Reported duration is less than one week. The patient reported no systemic symptoms. The patient described the issue as a rash. Close-up view. The affected area is the back of the torso and front of the torso. Female patient, age 60–69. Fitzpatrick phototype I. The lesion is described as raised or bumpy. Symptoms reported: bothersome appearance:
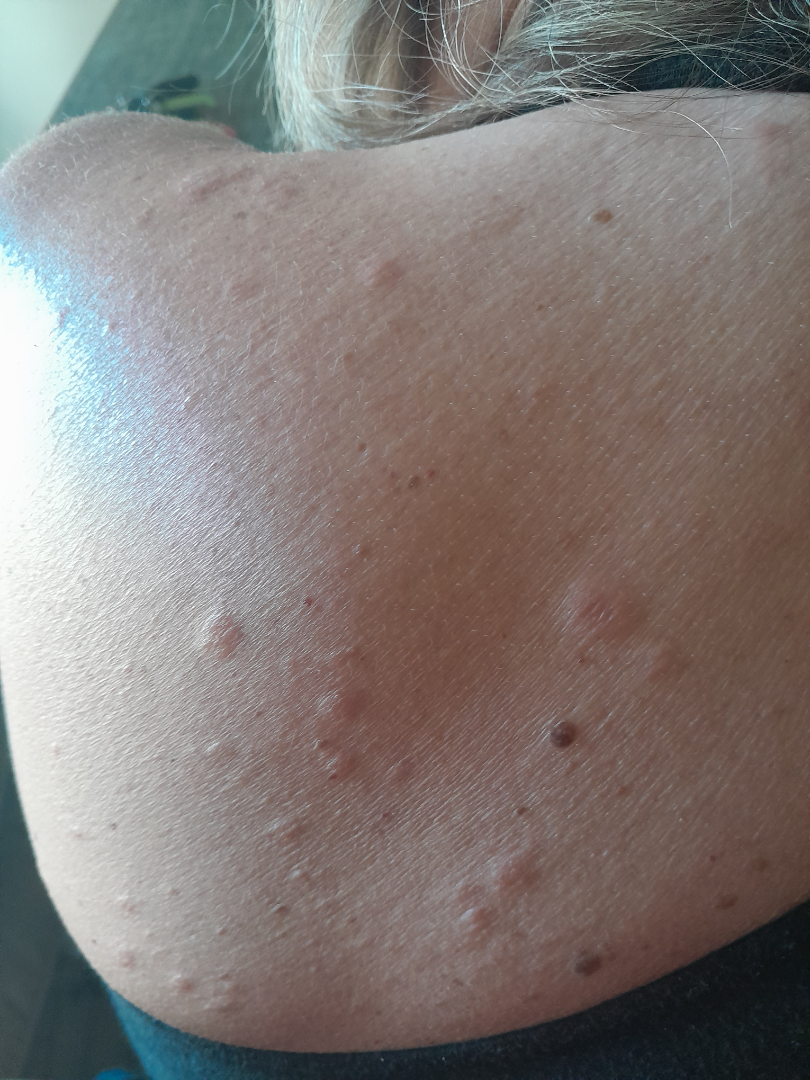Review: The leading impression is Pityriasis rosea.